The lesion is described as rough or flaky, fluid-filled and raised or bumpy; a close-up photograph; the condition has been present for about one day; the patient is a female aged 30–39; Fitzpatrick III; the patient described the issue as a rash:
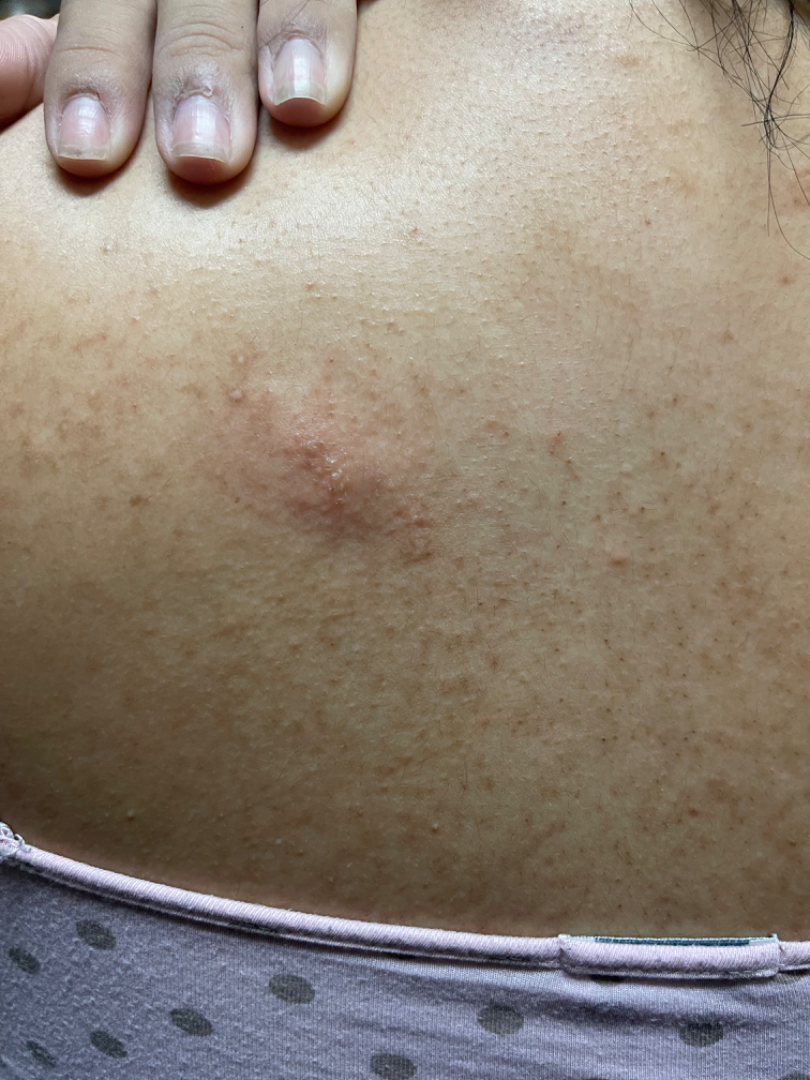assessment: ungradable on photographic review.